A dermoscopy image of a single skin lesion:
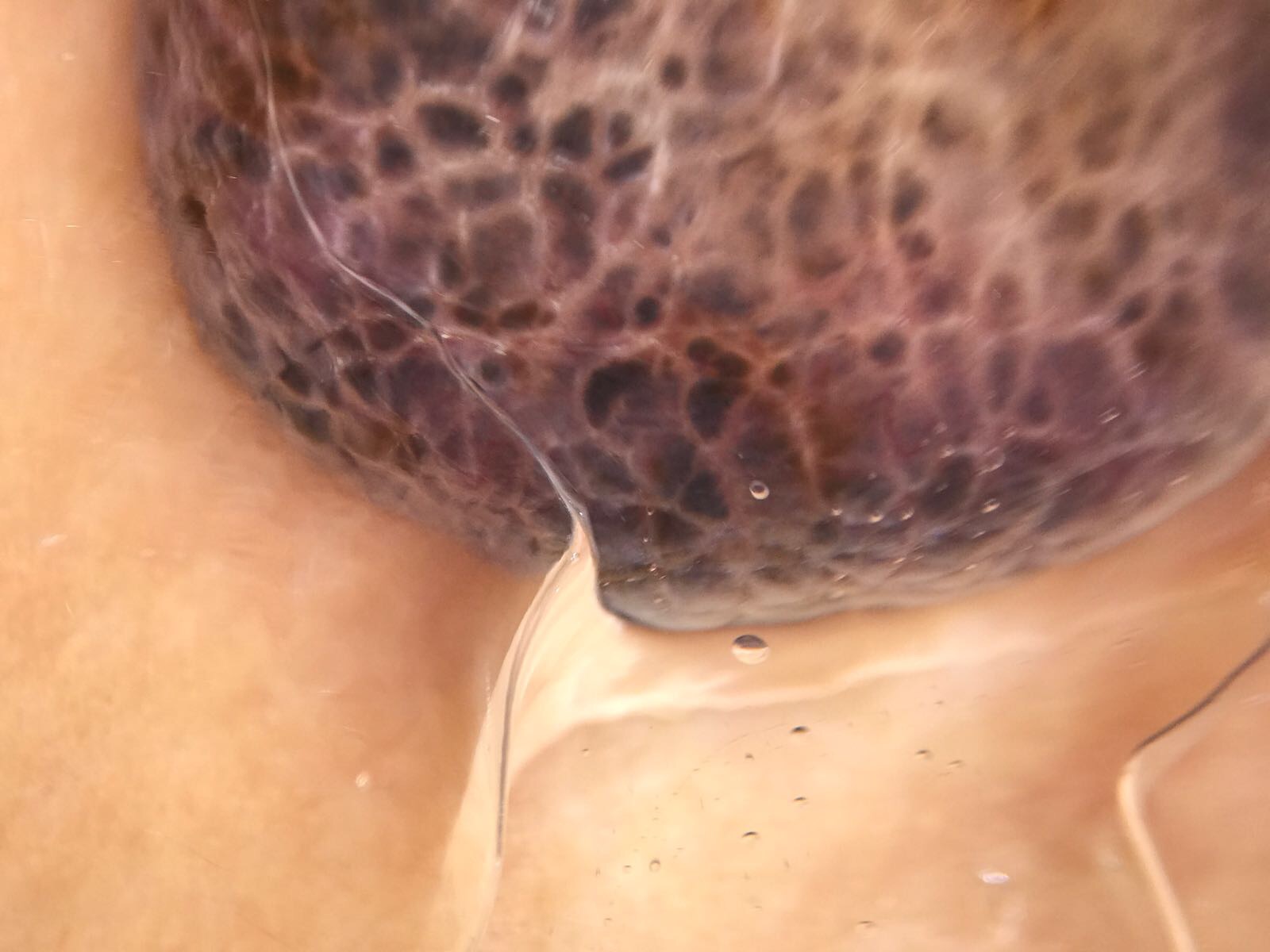label: melanoma (biopsy-proven).